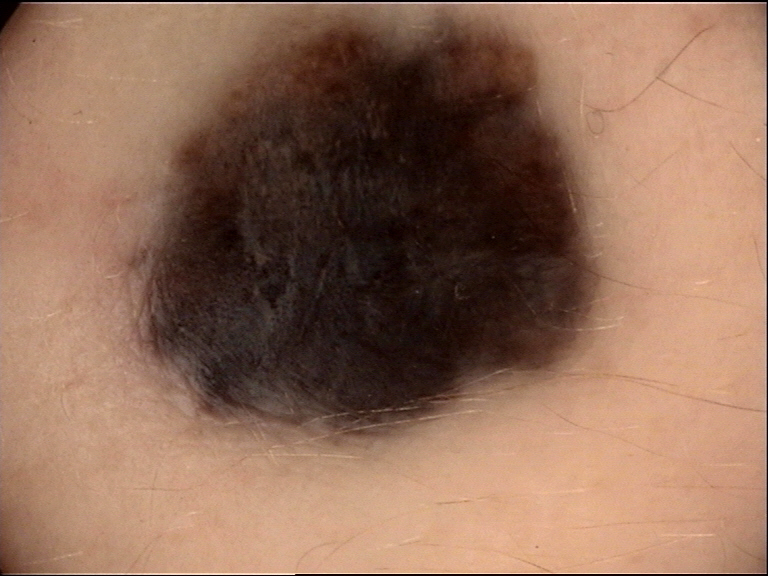Conclusion: Classified as a banal lesion — a blue nevus.